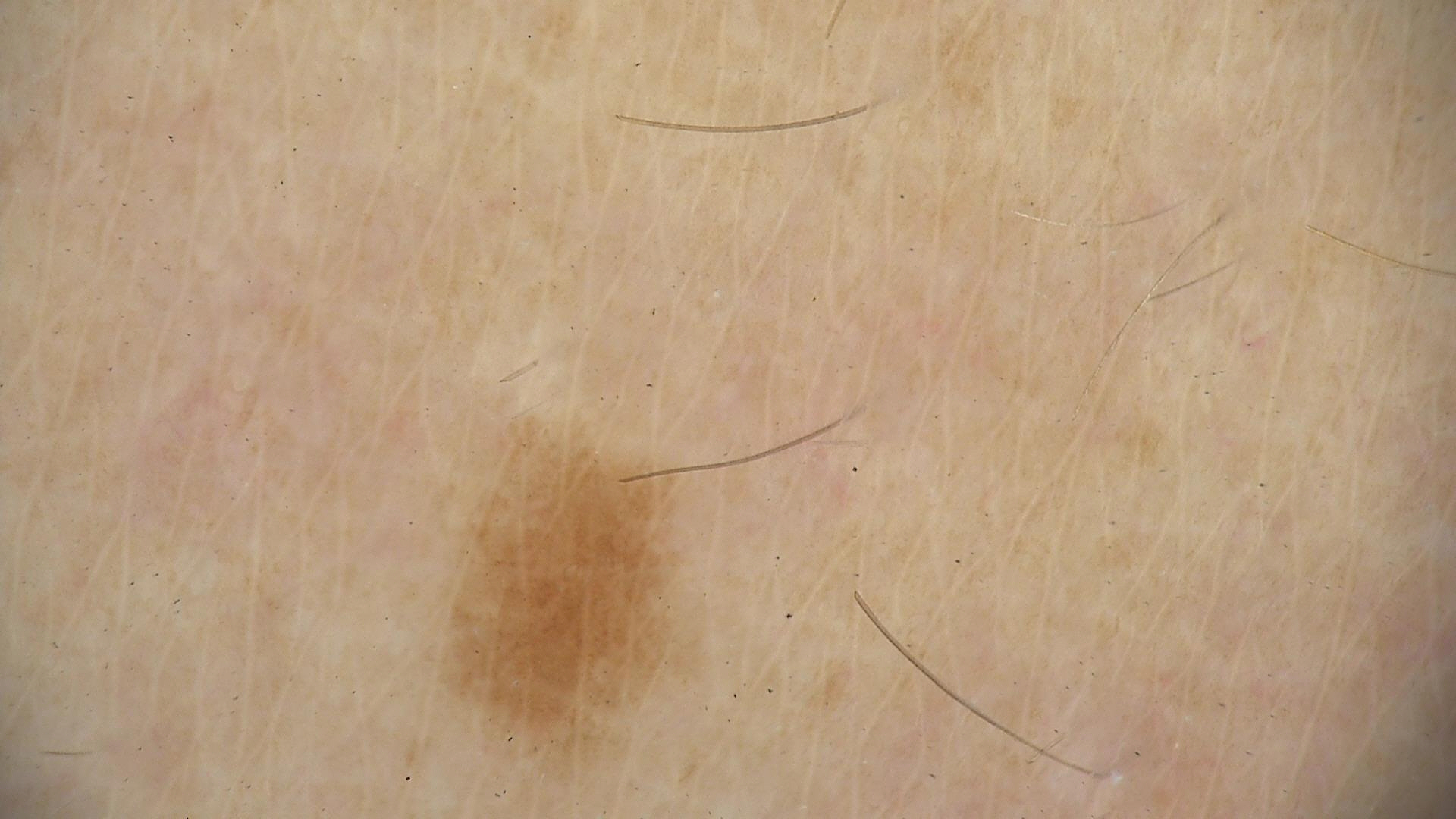A skin lesion imaged with a dermatoscope. The diagnostic label was a dysplastic junctional nevus.